Close-up view; the arm is involved: 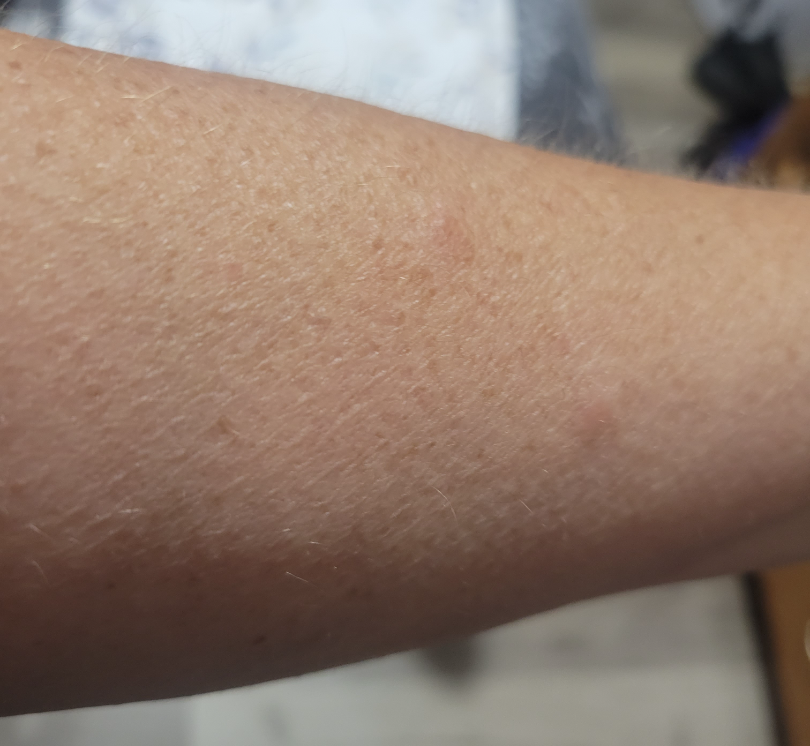Impression:
The image was not sufficient for the reviewer to characterize the skin condition.
History:
The contributor notes the lesion is raised or bumpy. The condition has been present for less than one week. Skin tone: Fitzpatrick phototype III; lay reviewers estimated a Monk skin tone scale of 3. Reported lesion symptoms include itching.